The patient is Fitzpatrick I. A female patient aged 56. A clinical photo of a skin lesion taken with a smartphone. The chart records prior malignancy (patient or family), no pesticide exposure, and no tobacco use: 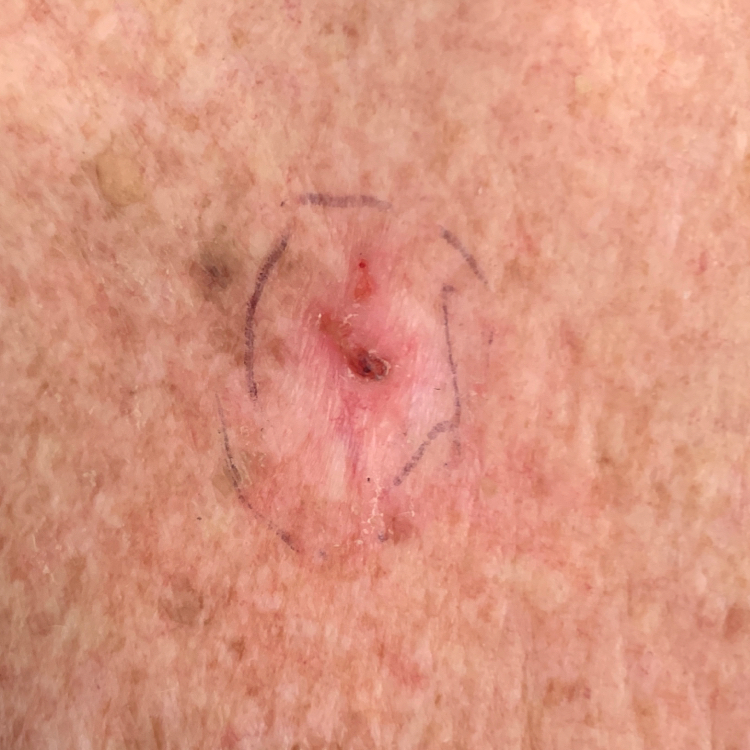Clinical context: The lesion was found on the chest. The lesion measures 15 × 15 mm. By the patient's account, the lesion is elevated. Diagnosis: Biopsy-confirmed as a basal cell carcinoma.